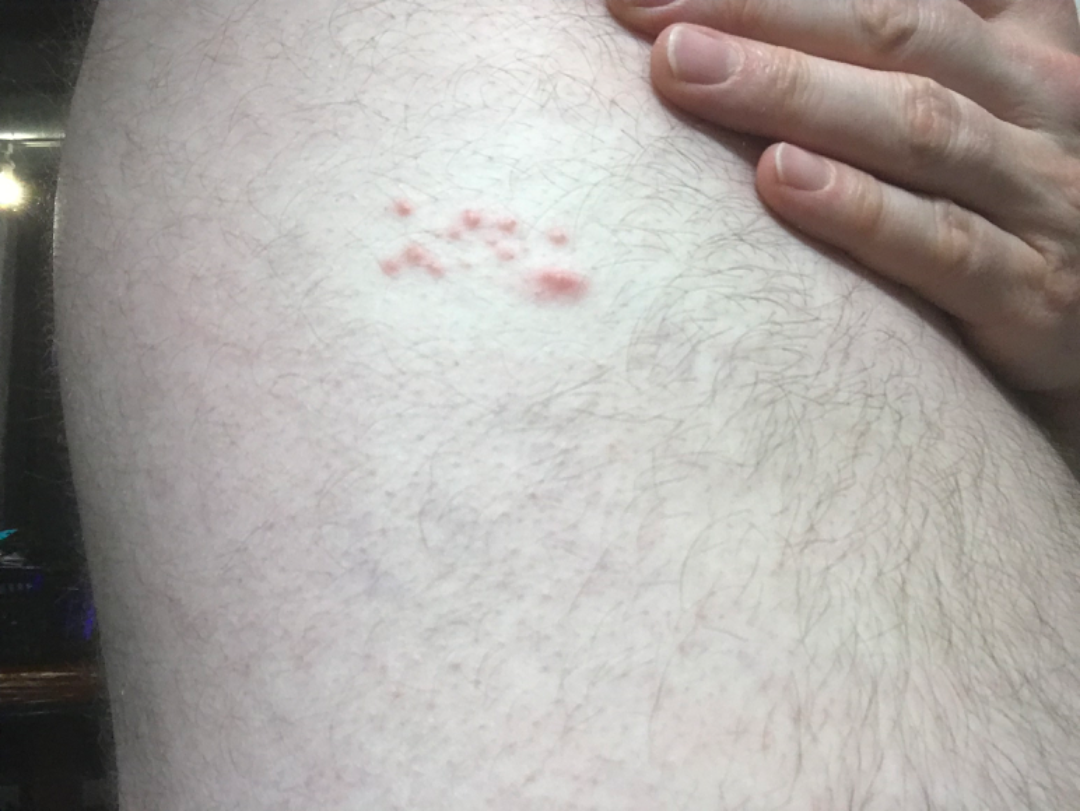assessment — indeterminate from the photograph; body site — front of the torso; photo taken — at a distance.